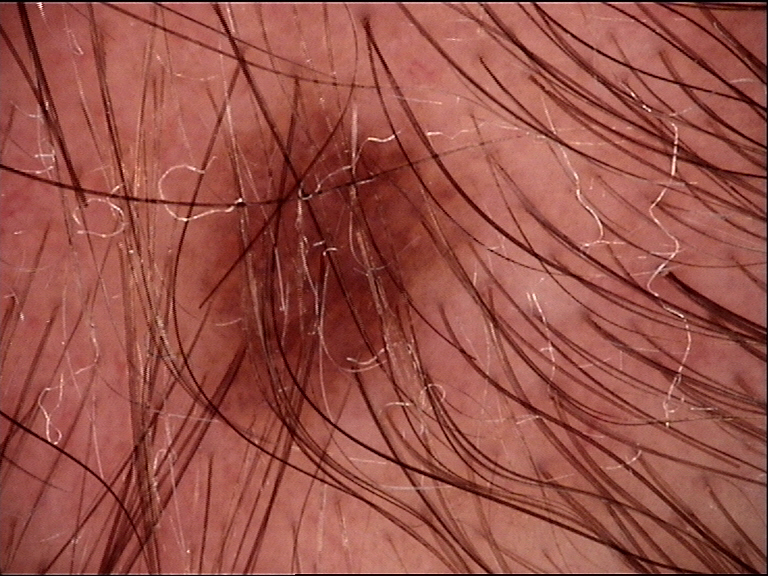imaging=dermoscopy; class=dysplastic junctional nevus (expert consensus).